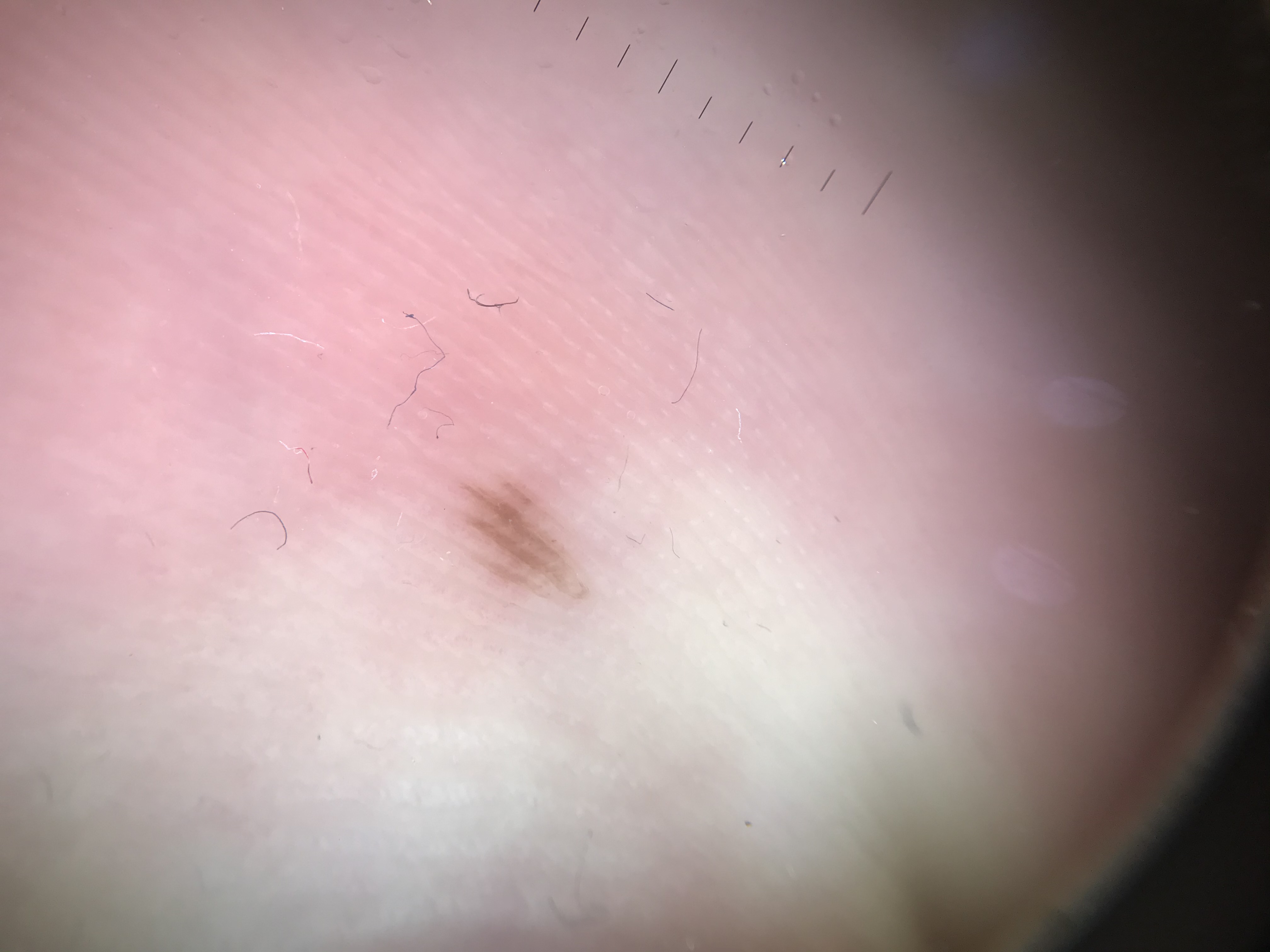Consistent with a benign lesion — an acral dysplastic junctional nevus.